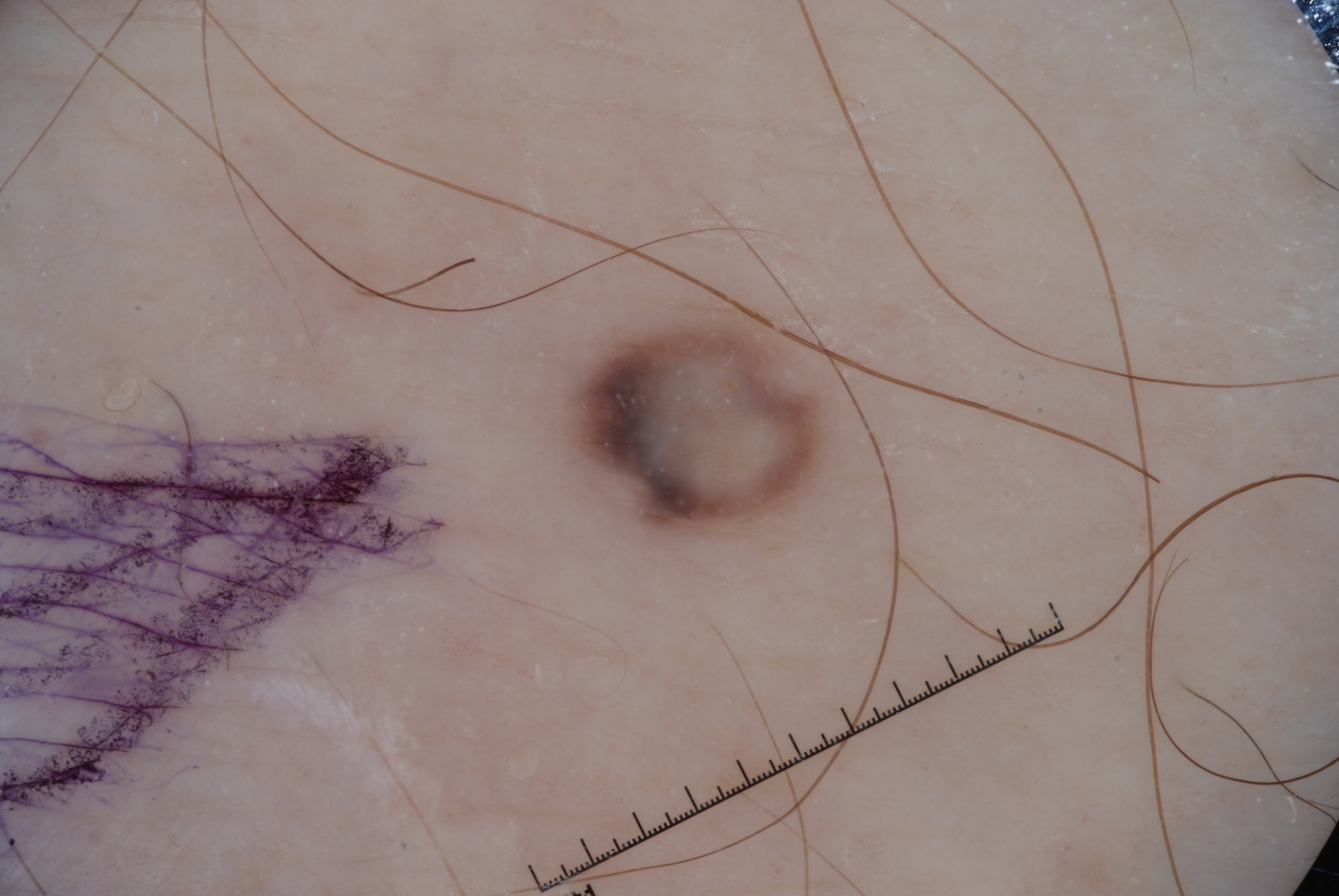A dermatoscopic image of a skin lesion. Dermoscopy demonstrates pigment network and milia-like cysts. The lesion takes up about 4% of the image. The lesion's extent is x1=565, y1=301, x2=826, y2=539. Clinically diagnosed as a melanocytic nevus.